The patient reports the condition has been present for one to four weeks · the patient described the issue as a rash · this image was taken at an angle · the lesion is described as raised or bumpy · located on the arm · the patient reported no systemic symptoms: 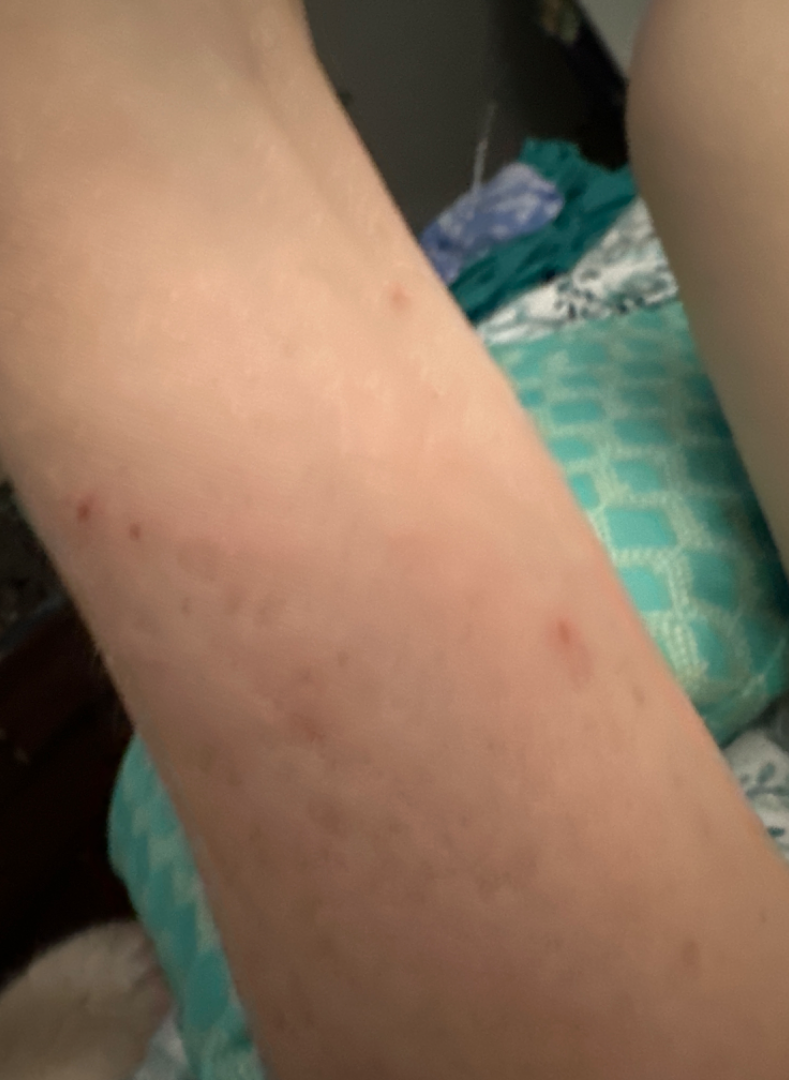| field | value |
|---|---|
| assessment | indeterminate |